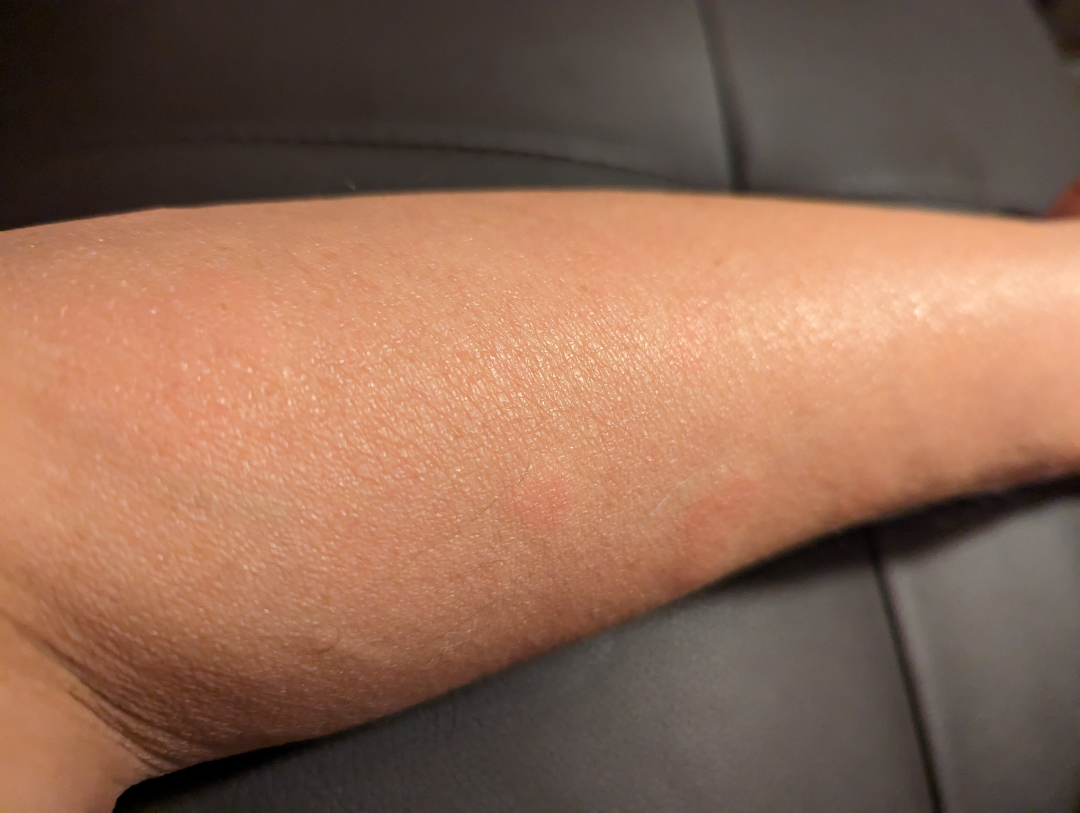shot type: close-up
texture: raised or bumpy
reported symptoms: none reported
present for: one to three months
patient: male
affected area: leg, arm and back of the hand
differential diagnosis: Urticaria (most likely)